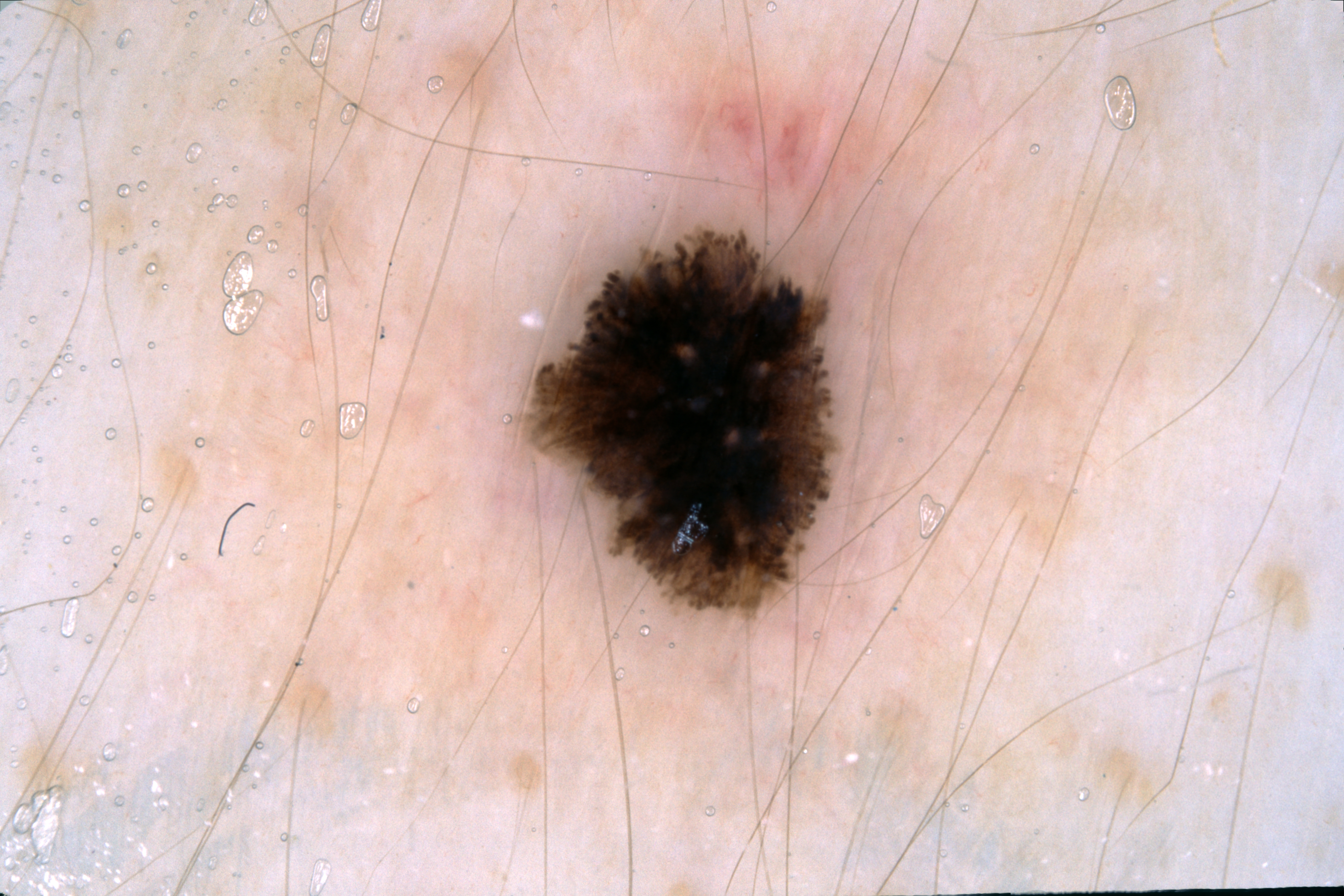- image — dermatoscopic image of a skin lesion
- bounding box — box(529, 230, 835, 610)
- lesion size — ~7% of the field
- dermoscopic findings — streaks; absent: pigment network, milia-like cysts, and negative network
- diagnosis — a melanocytic nevus